A skin lesion imaged with a dermatoscope.
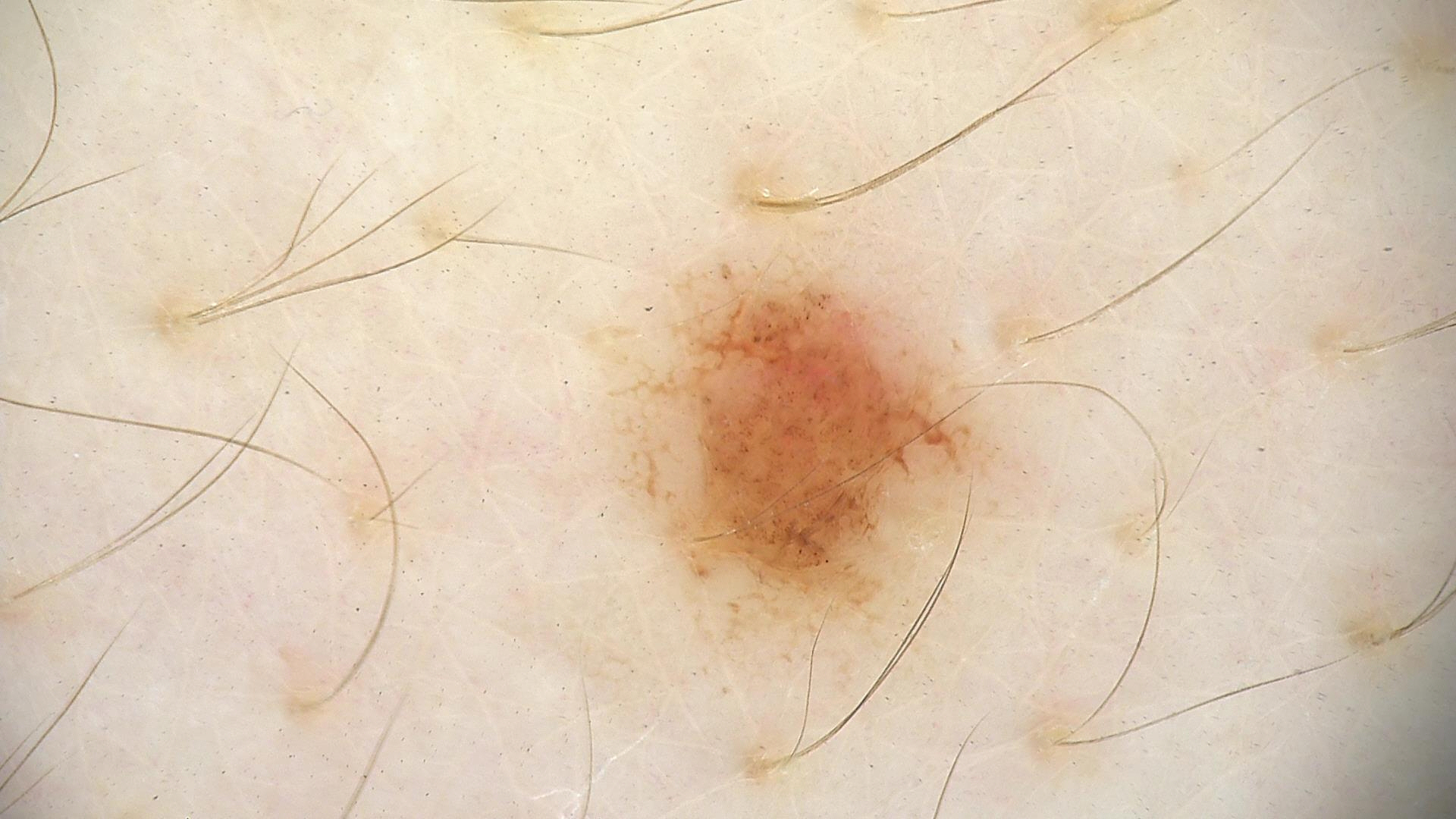Findings:
• class — dysplastic junctional nevus (expert consensus)